A skin lesion imaged with a dermatoscope:
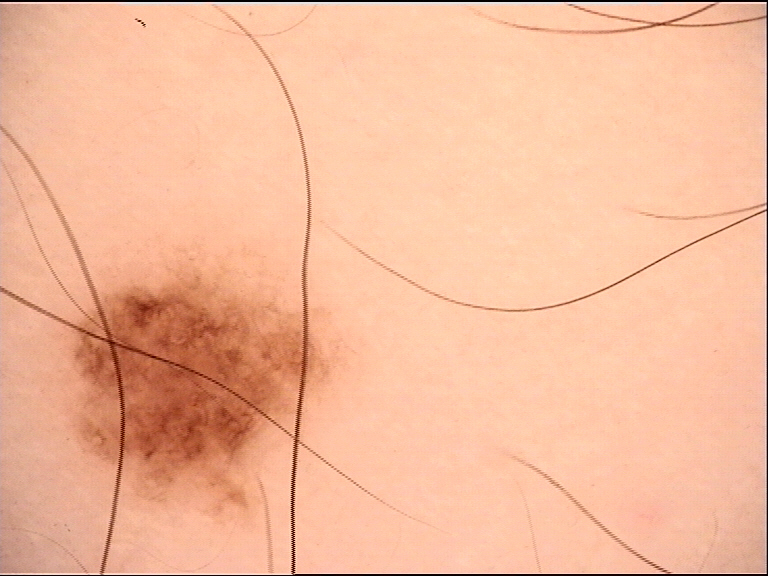Consistent with a banal lesion — a junctional nevus.